A male patient aged around 45; a dermoscopic close-up of a skin lesion:
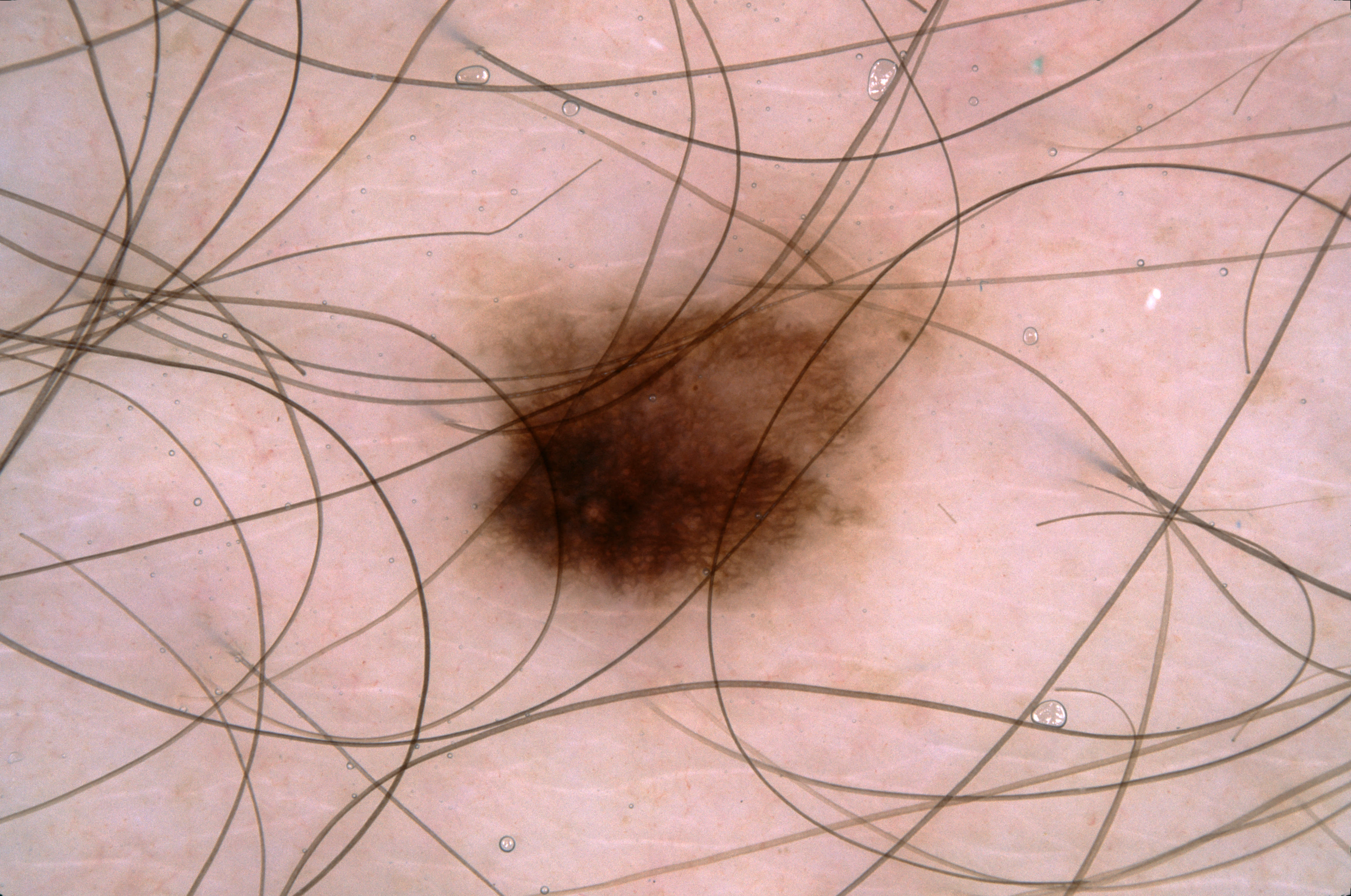Summary: The lesion's extent is left=433, top=182, right=966, bottom=611. Dermoscopically, the lesion shows pigment network, with no milia-like cysts, streaks, or negative network. Impression: The clinical diagnosis was a melanocytic nevus.